Reported duration is less than one week; the photograph is a close-up of the affected area; the lesion involves the leg; no relevant systemic symptoms; the lesion is described as fluid-filled and raised or bumpy:
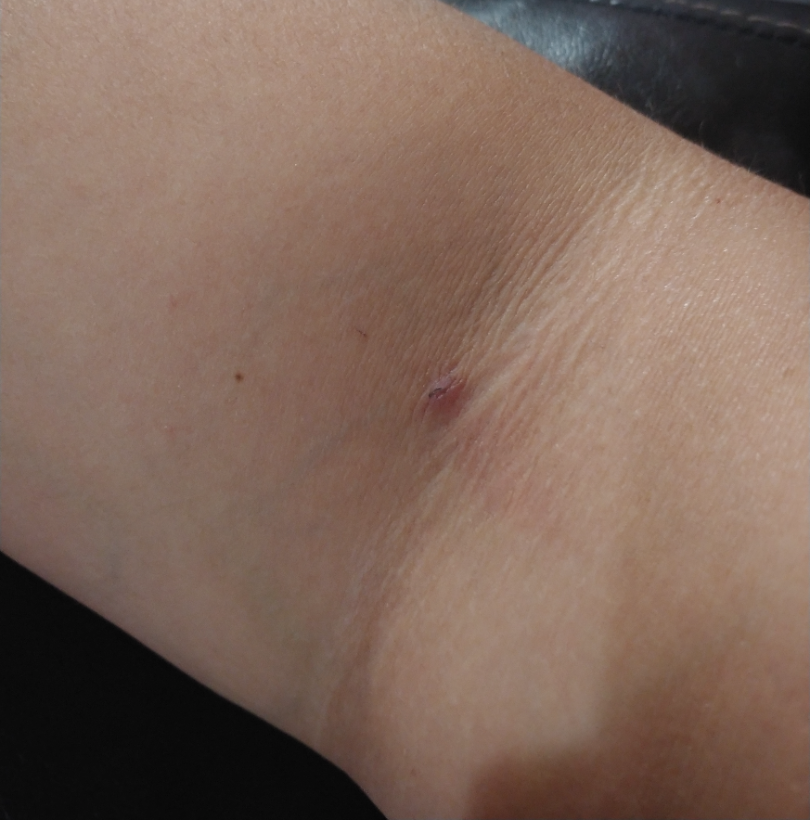Notes:
– assessment — could not be assessed